A dermatoscopic image of a skin lesion.
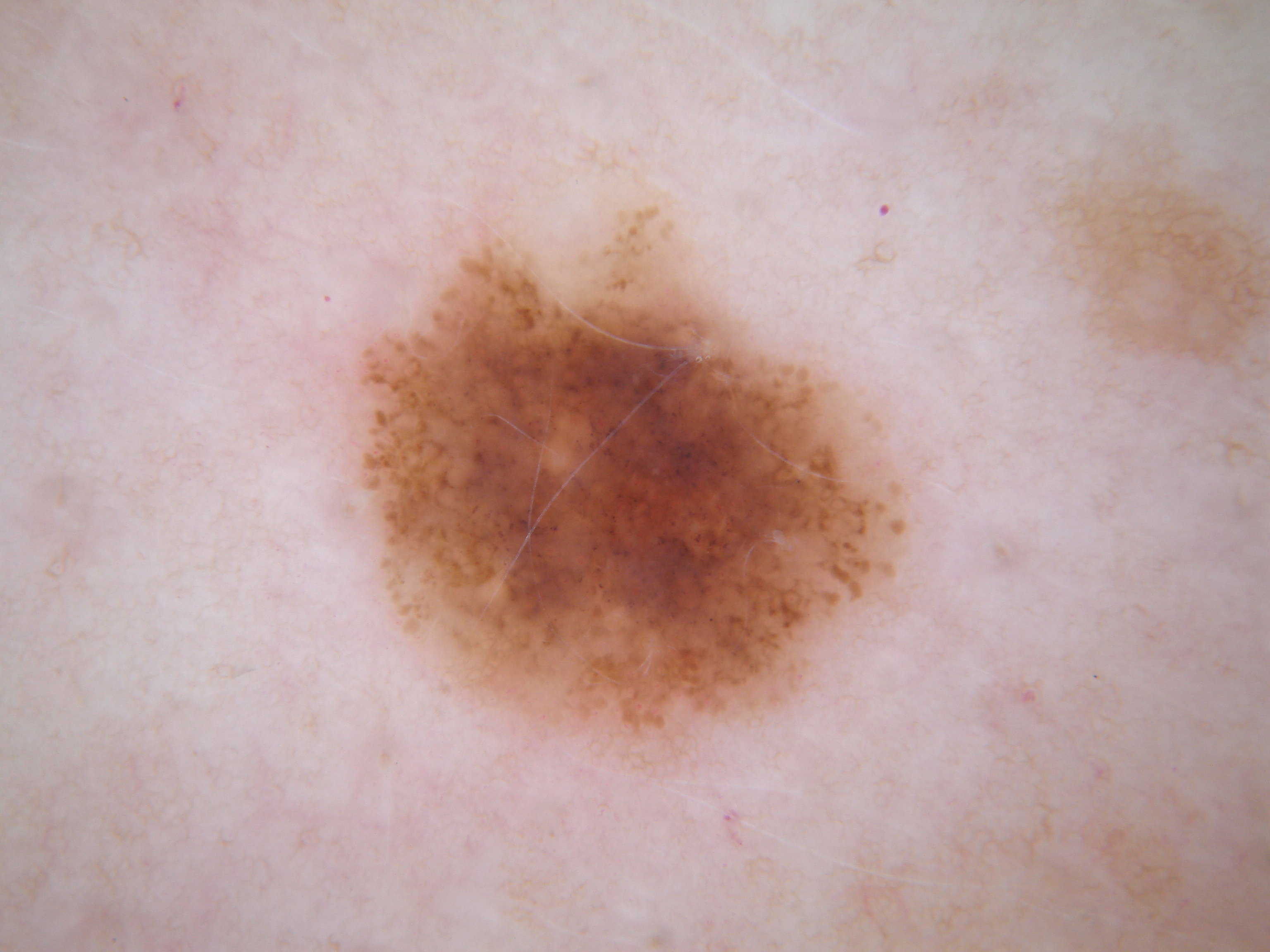On dermoscopy, the lesion shows pigment network, streaks, and globules; no milia-like cysts or negative network. The visible lesion spans left=347, top=204, right=913, bottom=771. The lesion occupies roughly 17% of the field. Expert review diagnosed this as a melanocytic nevus.